A skin lesion imaged with a dermatoscope · a female subject aged approximately 60 — 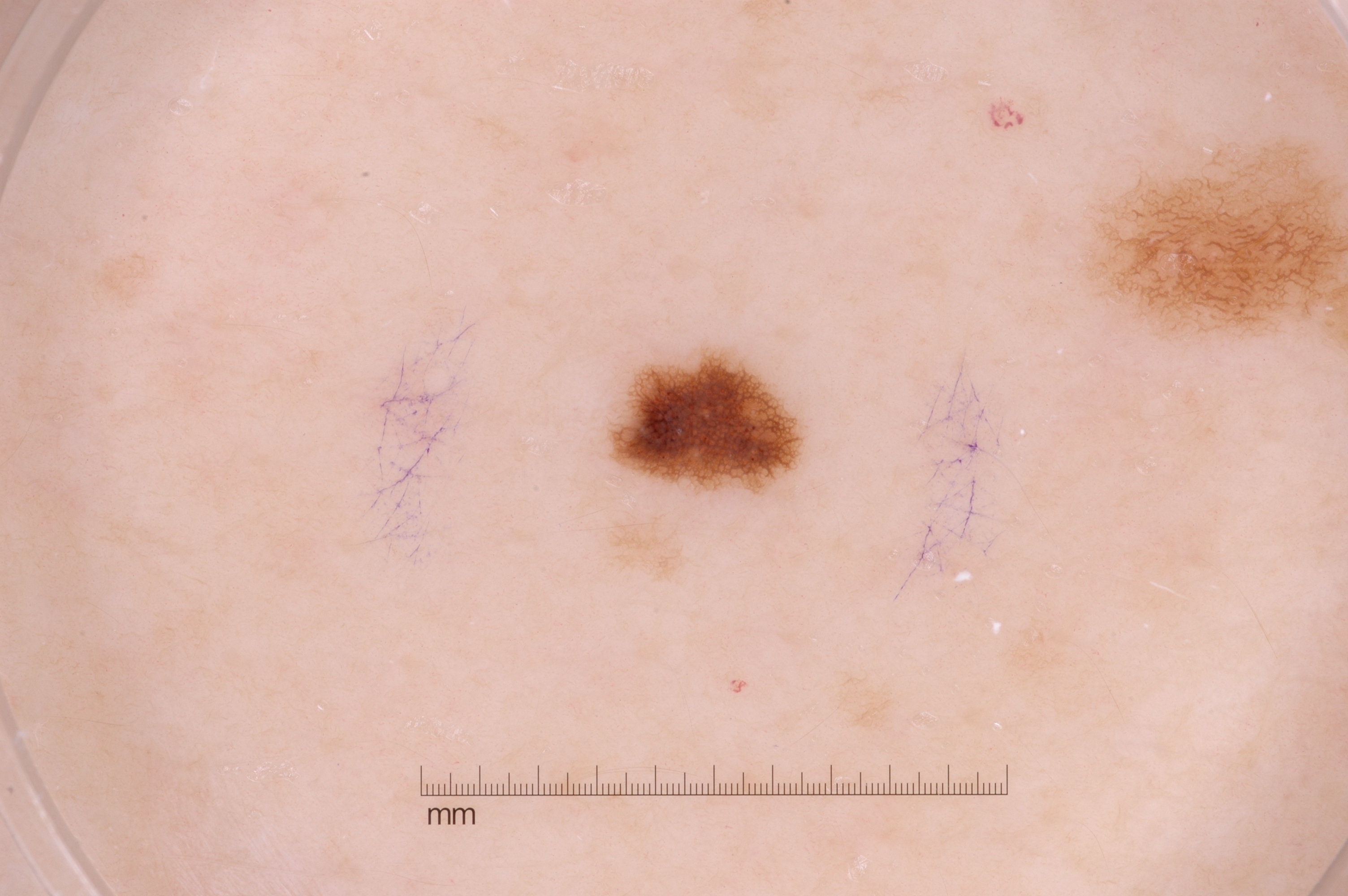features: pigment network
lesion bbox: 605/345/807/497
lesion extent: small
impression: a melanocytic nevus, a benign skin lesion